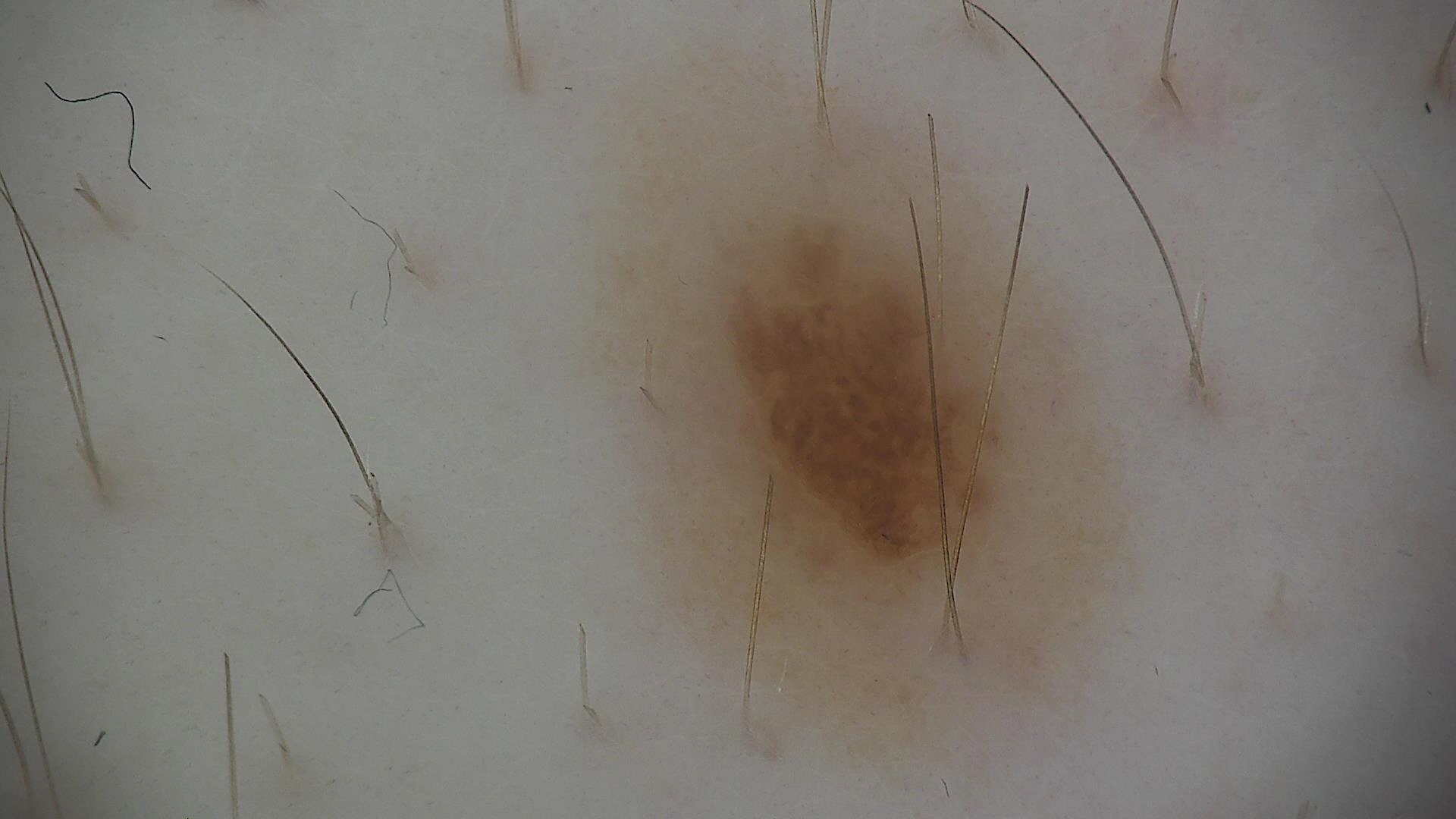The diagnostic label was a dysplastic compound nevus.